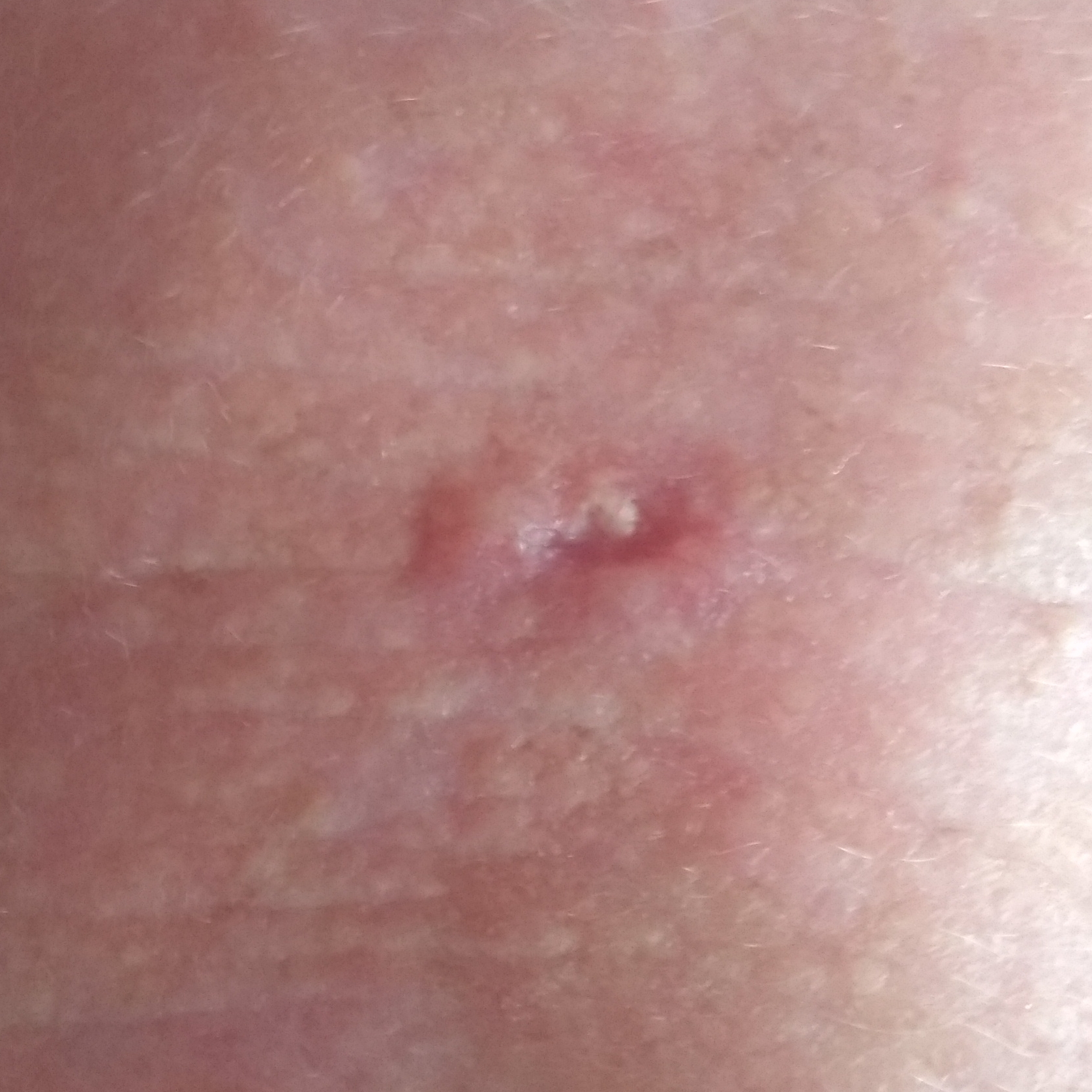The patient is Fitzpatrick phototype II. A female subject aged 66. A clinical photograph showing a skin lesion. The lesion was found on the face. The lesion measures 12 × 8 mm. Biopsy-confirmed as a basal cell carcinoma.